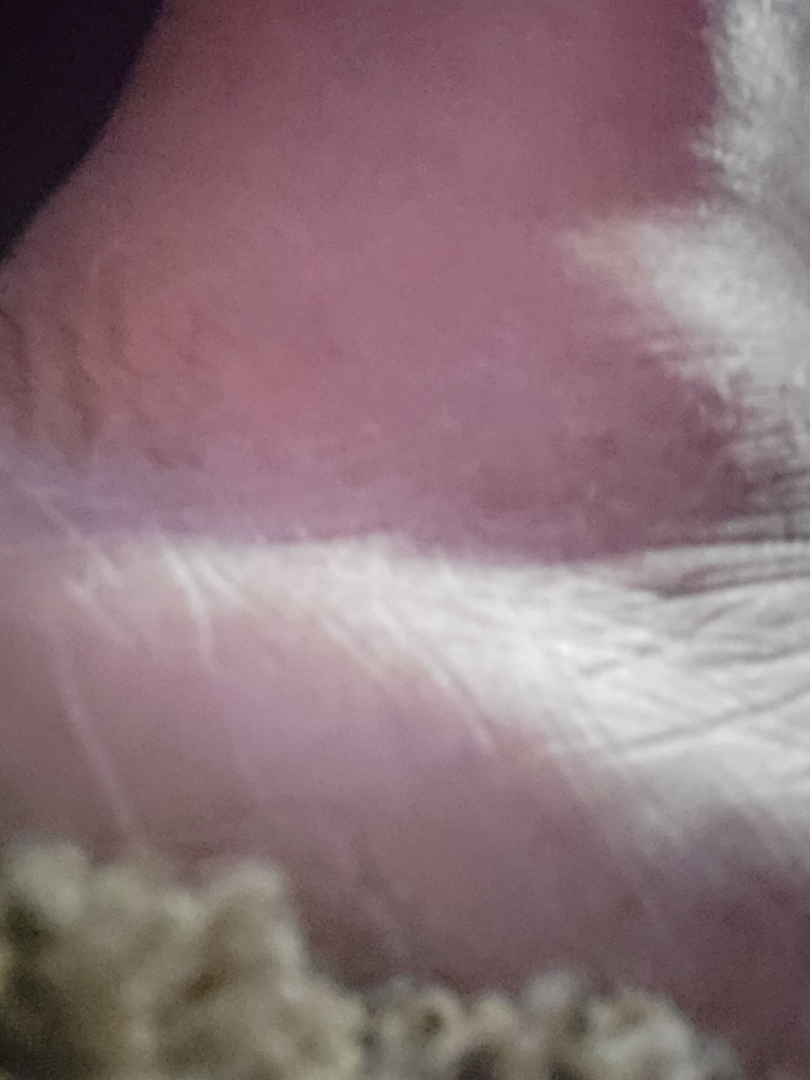Background: Fitzpatrick V. The patient reports the lesion is rough or flaky. Reported duration is more than one year. No associated lesion symptoms were reported. No associated systemic symptoms reported. A close-up photograph. The patient is 40–49, female. Located on the sole of the foot. Findings: On dermatologist assessment of the image: Tinea and Eczema were considered with similar weight; less likely is Psoriasis.